The patient considered this skin that appeared healthy to them. The photograph was taken at an angle. The lesion involves the arm. Texture is reported as flat. Symptoms reported: darkening:
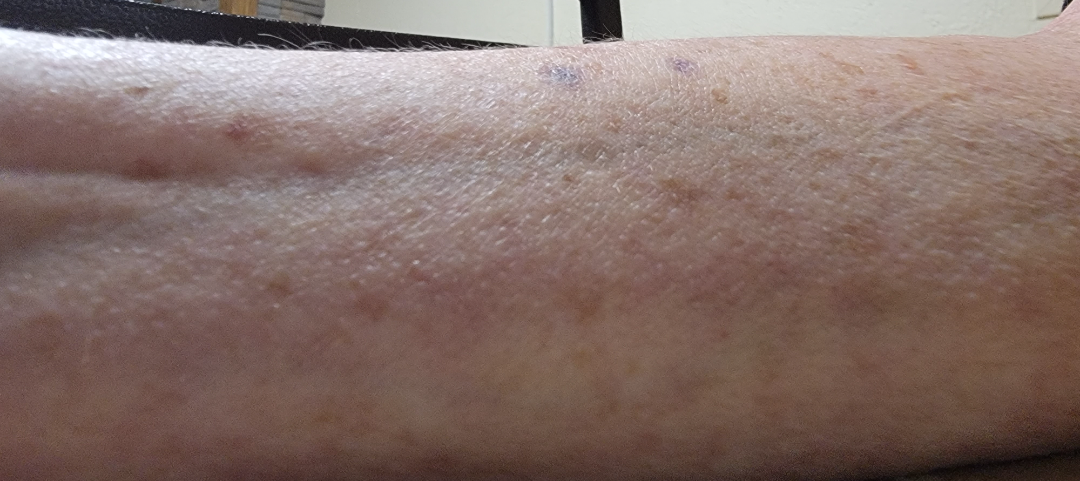– impression: ecchymoses (primary)